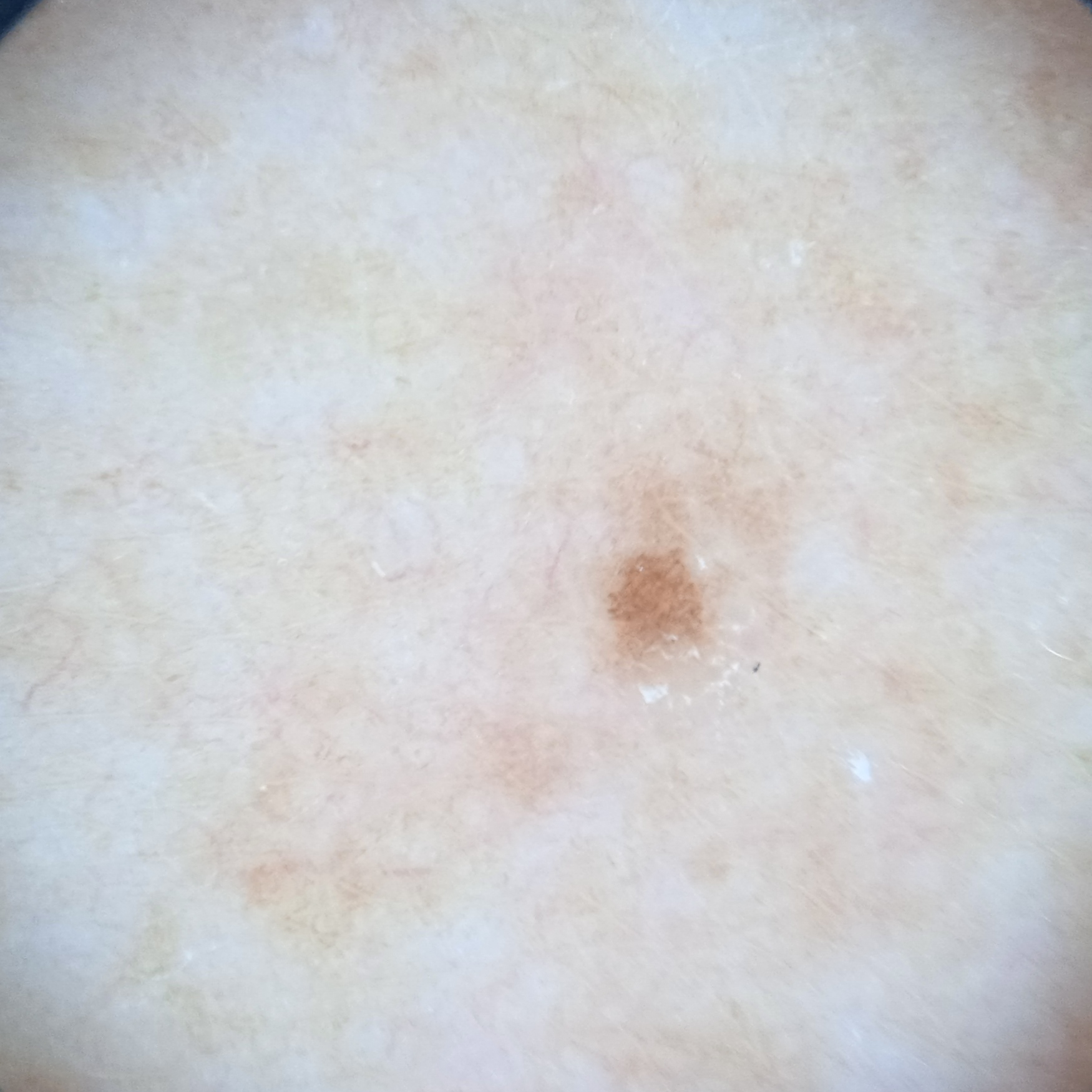{"referral": "research study (no referral diagnosis)", "diagnosis": {"name": "melanocytic nevus", "malignancy": "benign"}}